The patient described the issue as a nail problem. The contributor notes pain and bothersome appearance. Located on the palm. The contributor notes the condition has been present for one to four weeks. Female patient, age 40–49. The photo was captured at a distance. Skin tone: Fitzpatrick phototype II:
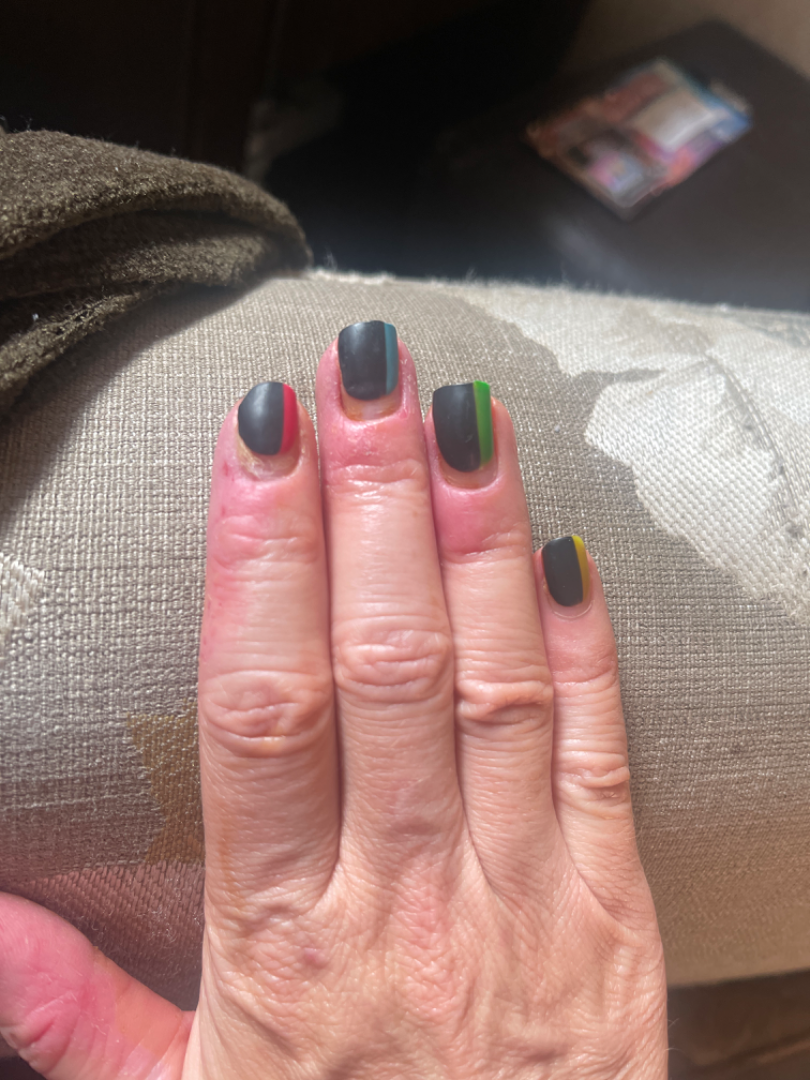{
  "differential": {
    "leading": [
      "Paronychia"
    ],
    "unlikely": [
      "Eczema",
      "Allergic Contact Dermatitis"
    ]
  }
}